The leg is involved · the lesion is described as rough or flaky and raised or bumpy · the patient is a female aged 18–29 · the patient described the issue as a rash · no constitutional symptoms were reported · the photograph was taken at an angle.
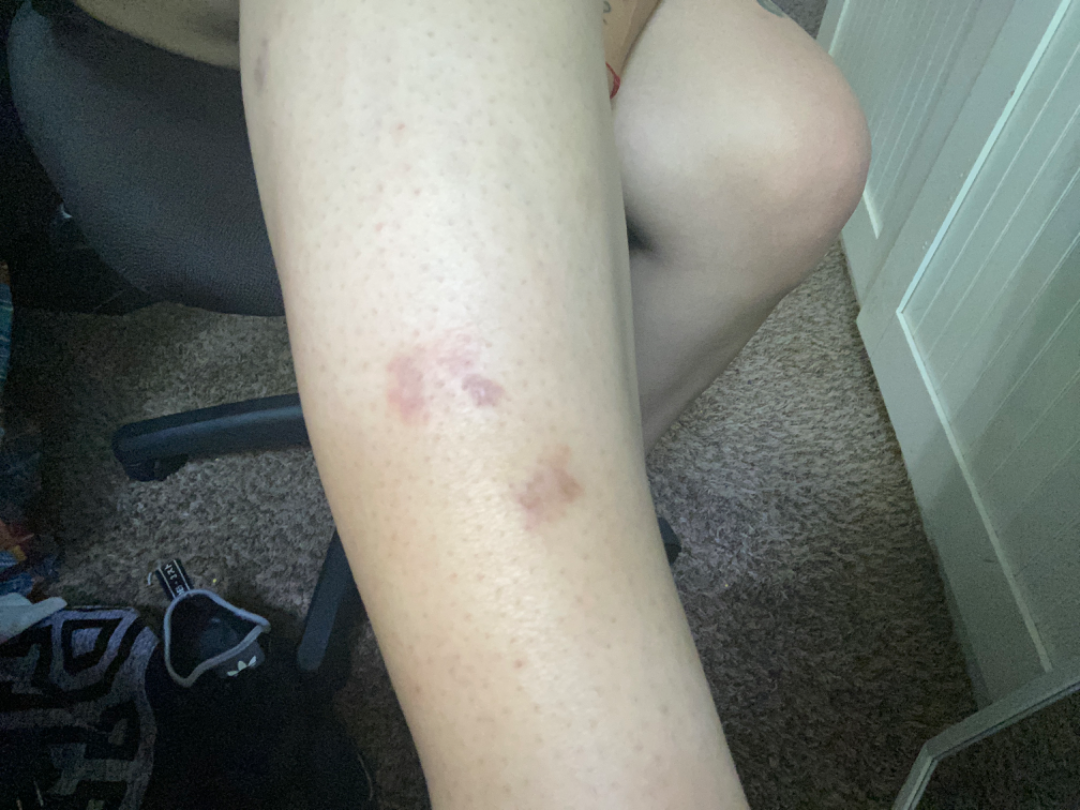Q: Could the case be diagnosed?
A: not assessable